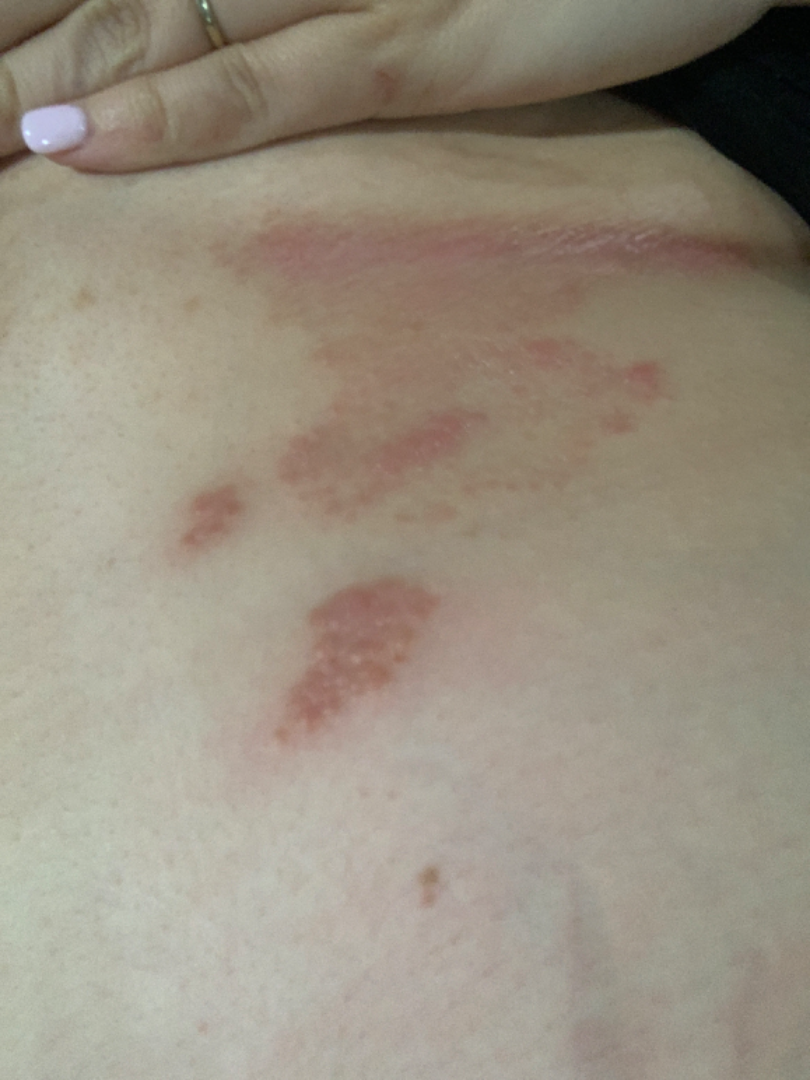Impression:
The reviewing clinician's impression was: Tinea (favored); Intertrigo (considered); Psoriasis (lower probability).